A female patient, aged approximately 65. A dermatoscopic image of a skin lesion — 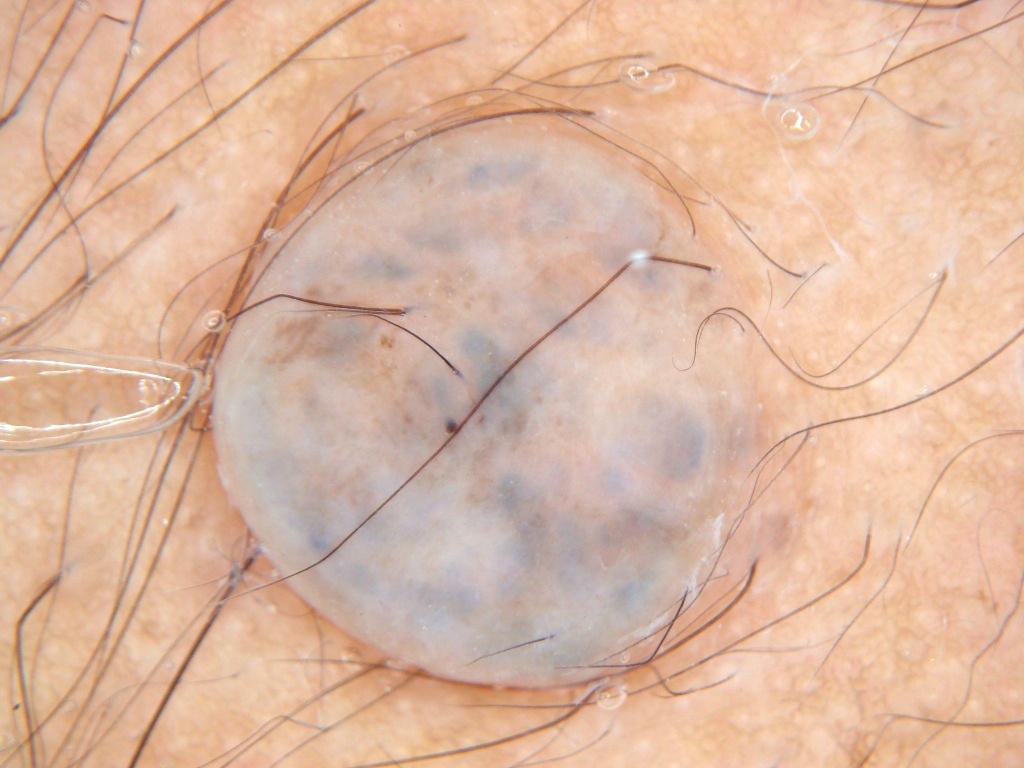Q: Where is the lesion located?
A: [212, 106, 813, 688]
Q: Which dermoscopic features were noted?
A: milia-like cysts
Q: How much of the field does the lesion occupy?
A: large
Q: What is the diagnosis?
A: a melanocytic nevus